This image was taken at a distance.
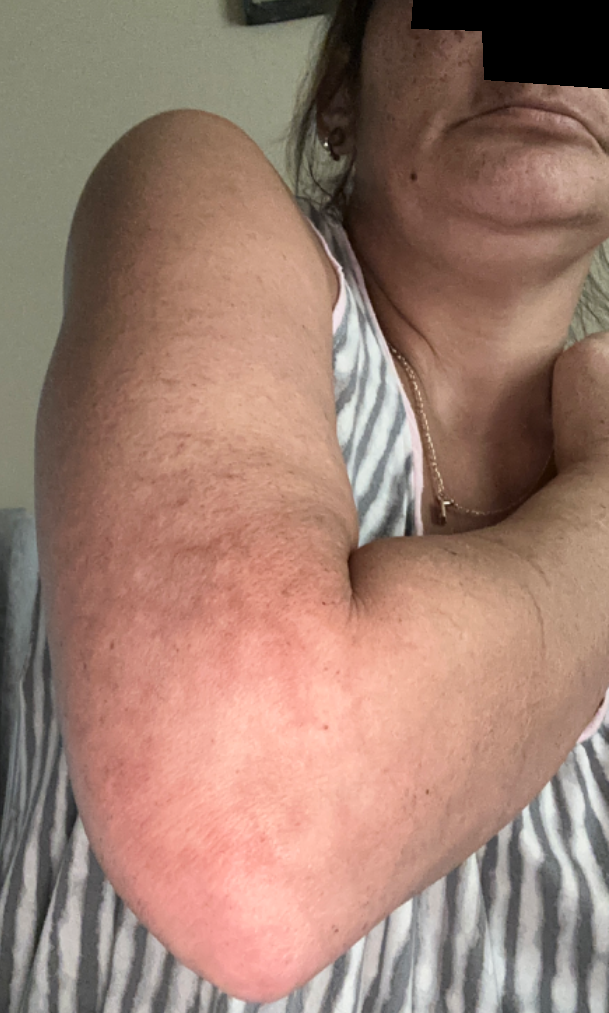The condition could not be reliably identified from the image.